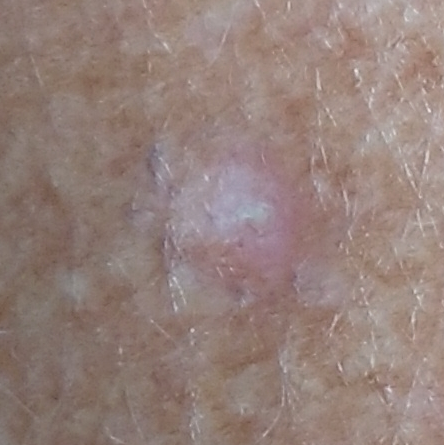Clinical context: A male subject aged 48. The lesion is on the back. The patient describes that the lesion itches. Conclusion: Confirmed on histopathology as an actinic keratosis.